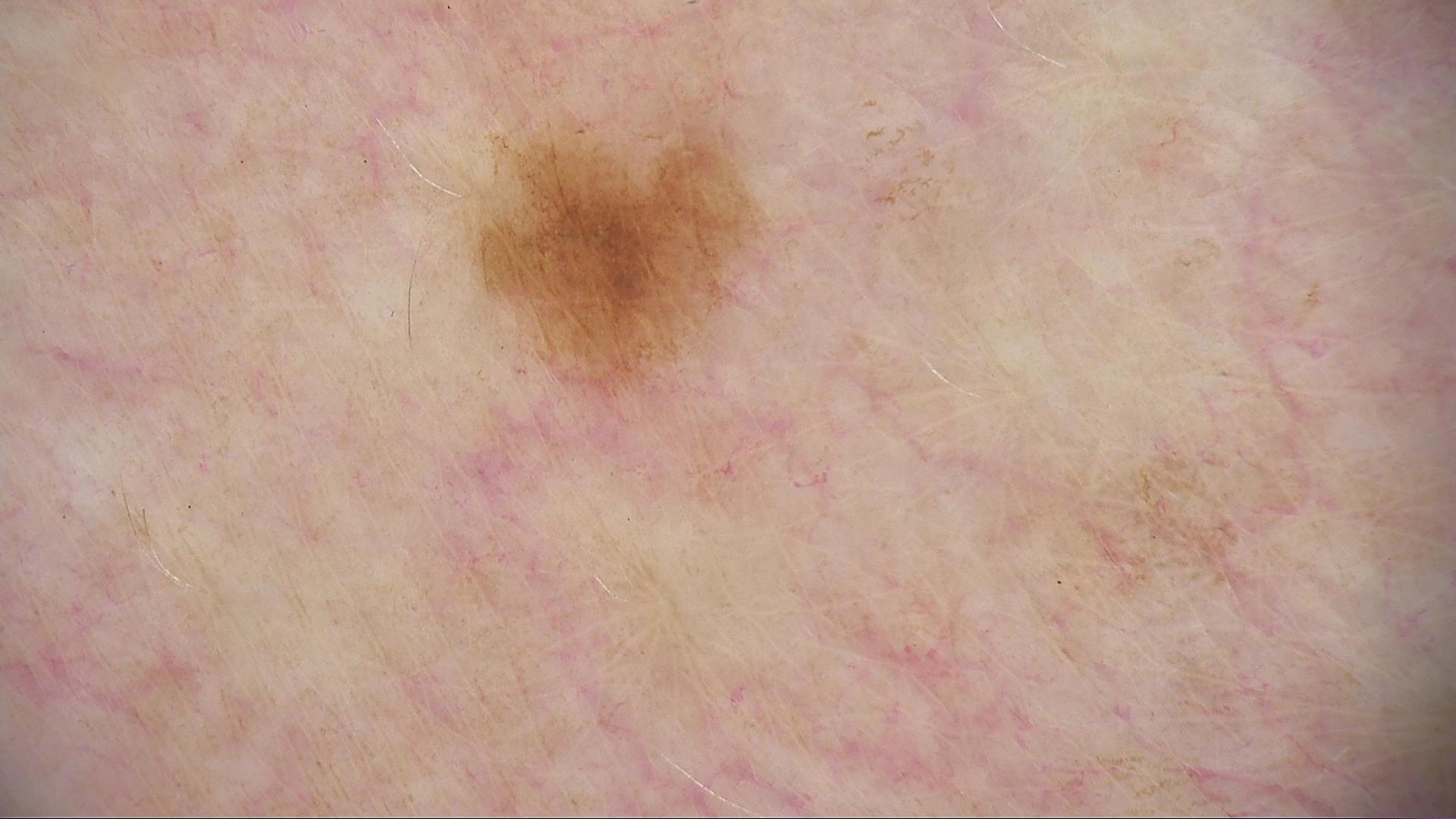image: dermatoscopy; lesion type: banal; diagnostic label: junctional nevus (expert consensus).